A skin lesion imaged with a dermatoscope. A female patient age 67. Collected as part of a research study, without a referral diagnosis — 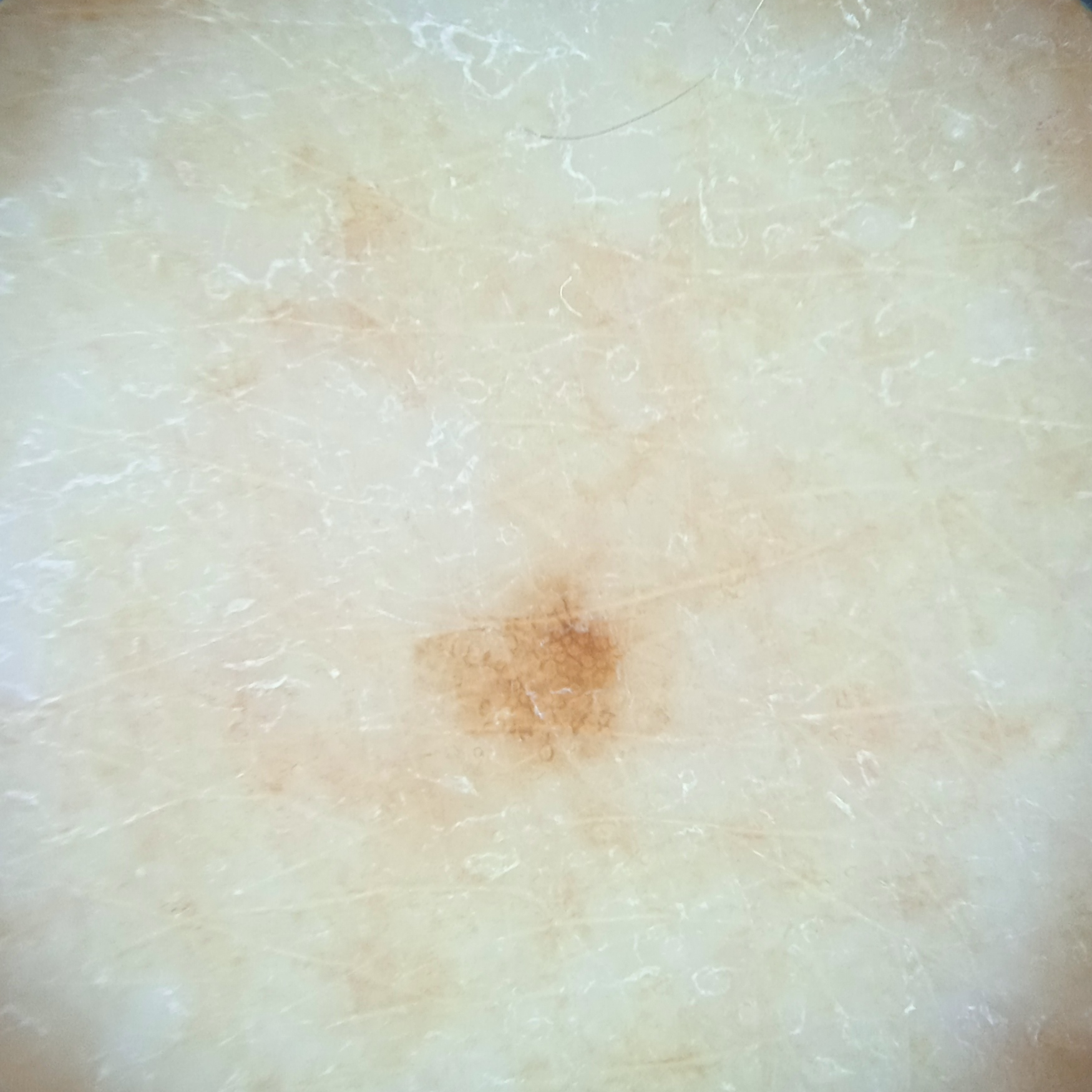Q: What is the anatomic site?
A: an arm
Q: How large is the lesion?
A: 2.1 mm
Q: What was the diagnosis?
A: melanocytic nevus (dermatologist consensus)